The head or neck, arm and leg are involved · female patient, age 18–29 · the patient indicates itching and bothersome appearance · present for less than one week · the patient considered this a rash · an image taken at an angle · texture is reported as raised or bumpy · no constitutional symptoms were reported: 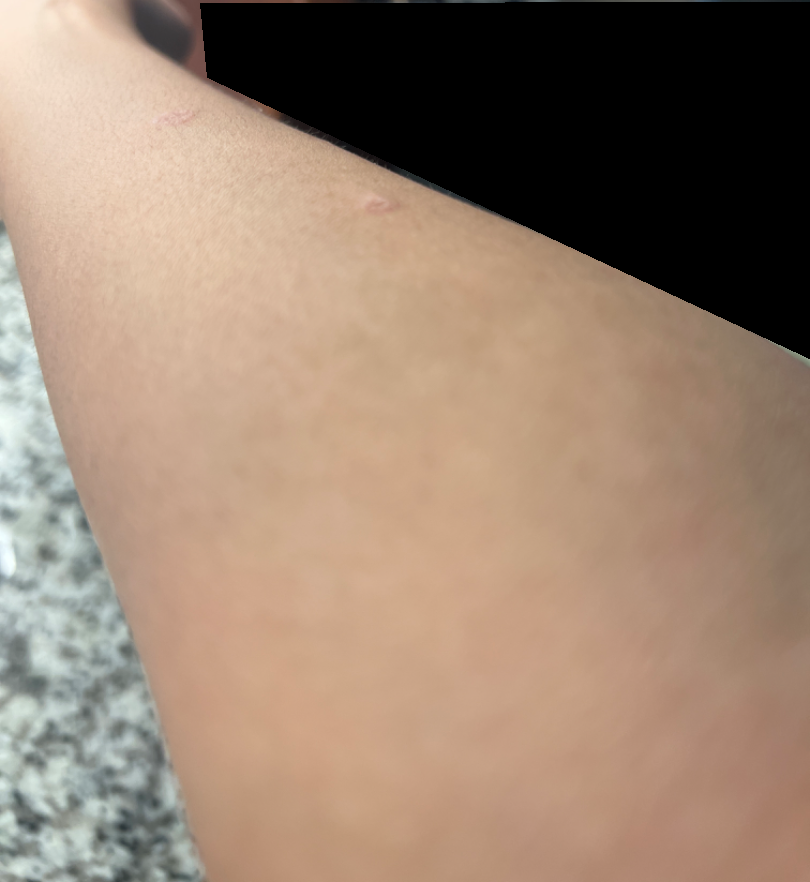On remote review of the image: Insect Bite (weight 1.00).